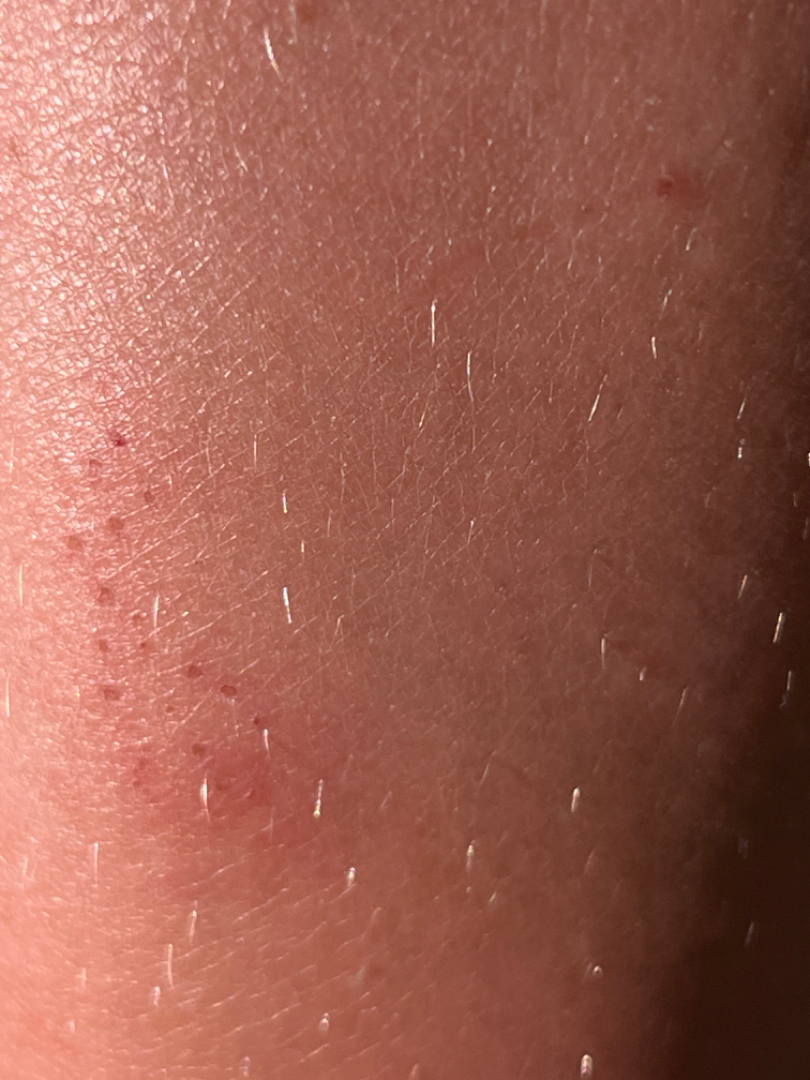No relevant systemic symptoms. Female subject, age 18–29. This is a close-up image. Skin tone: Fitzpatrick skin type V. The contributor reports burning and itching. The patient described the issue as a rash. The lesion involves the leg. The contributor reports the condition has been present for less than one week. On teledermatology review, in keeping with Eczema.